Fitzpatrick II; non-clinician graders estimated Monk Skin Tone 2 or 3 (two reviewer pools) · a close-up photograph · the affected area is the arm · the patient indicates the lesion is raised or bumpy · the condition has been present for less than one week: 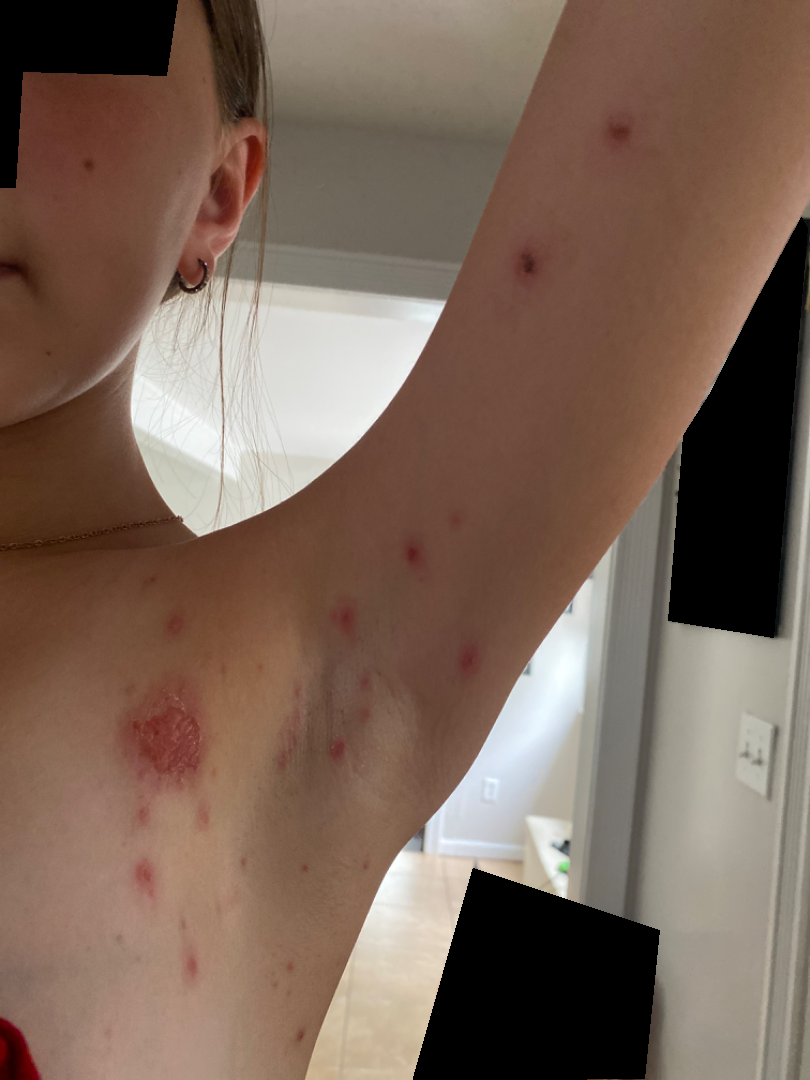Findings: Consistent with Impetigo.